Acquired for a research image collection, with no referral diagnosis; on a questionnaire the patient reported a personal history of cancer; a skin lesion imaged with a dermatoscope; the patient says their skin tans without first burning.
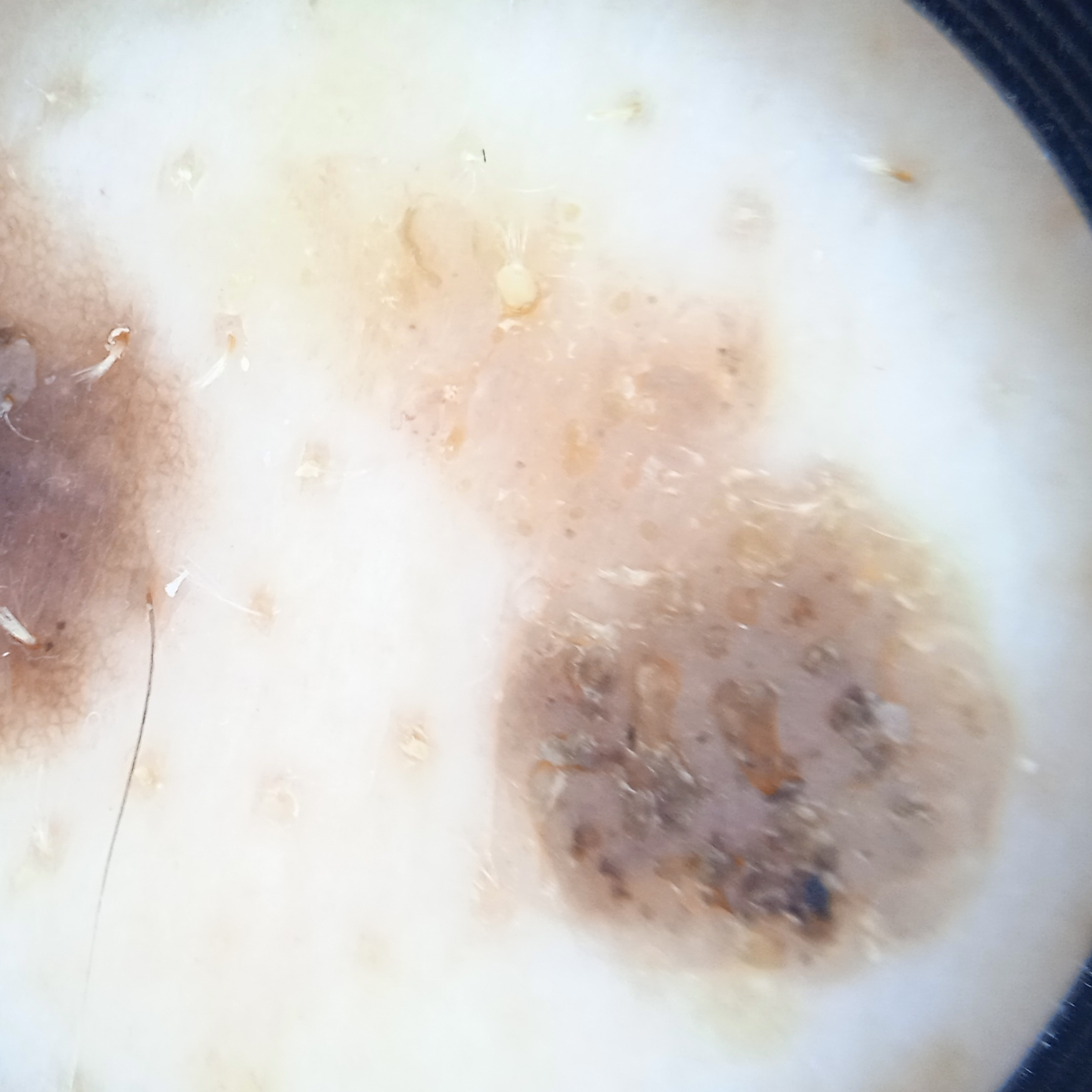The lesion measures approximately 10.3 mm.
Dermatologist review favored a seborrheic keratosis.